The photo was captured at an angle. The lesion involves the arm, head or neck, front of the torso, back of the torso and leg.
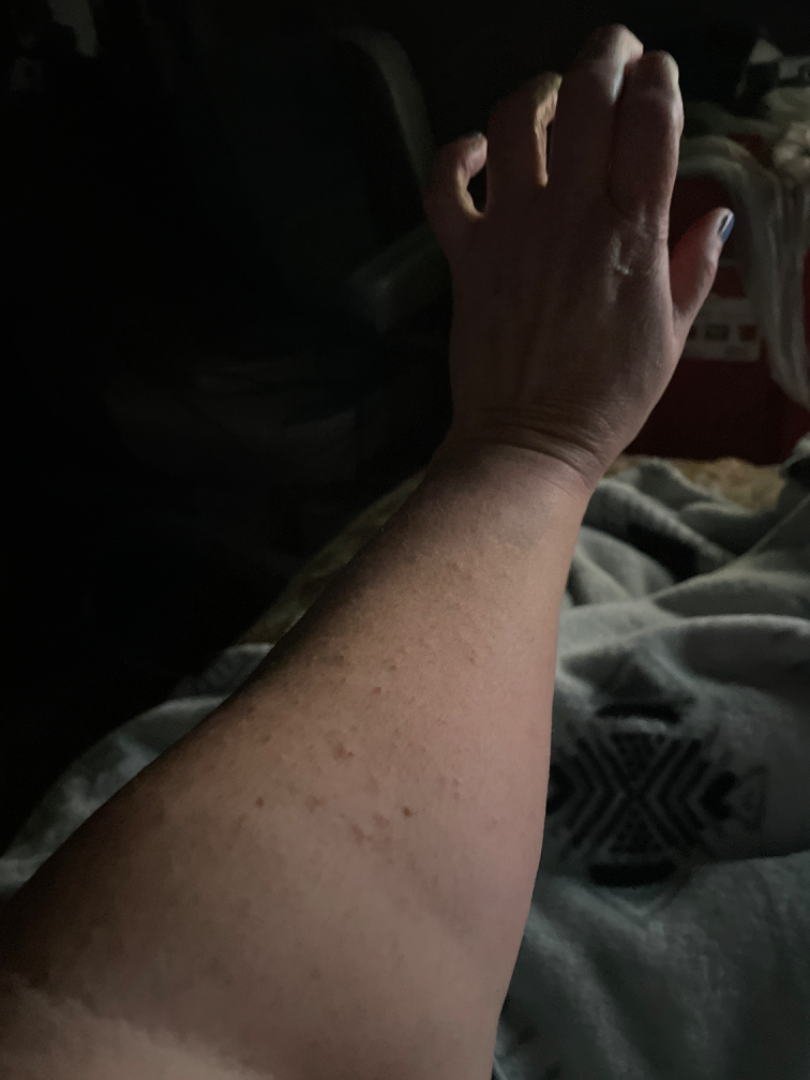The case was difficult to assess from the available photograph. The lesion is described as raised or bumpy. Symptoms reported: itching, burning and bothersome appearance. Reported duration is less than one week.